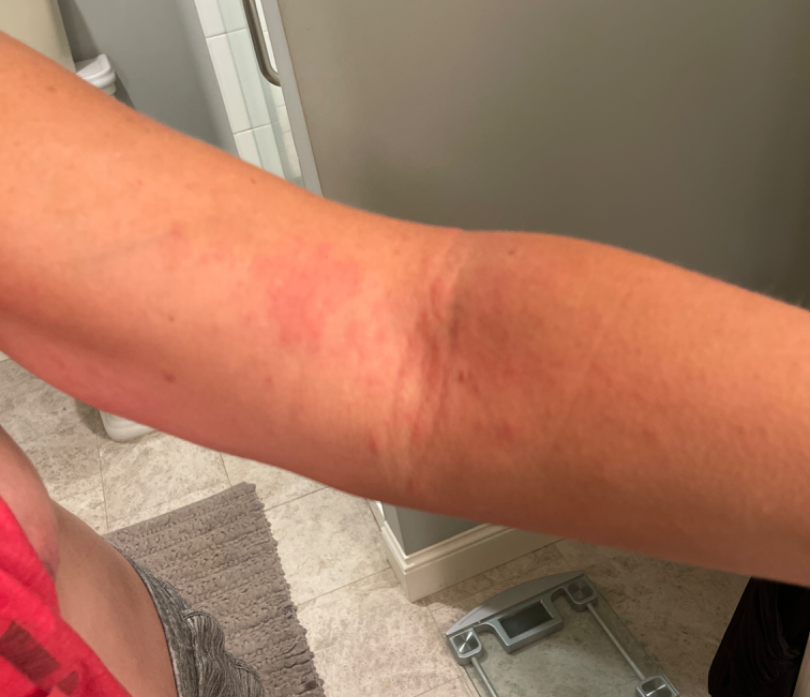self-categorized as = a rash
duration = less than one week
view = at a distance
patient-reported symptoms = itching
anatomic site = leg, back of the torso, arm, front of the torso and back of the hand
impression = the favored diagnosis is Allergic Contact Dermatitis; also on the differential is Eczema; less likely is Folliculitis